A dermatoscopic image of a skin lesion: 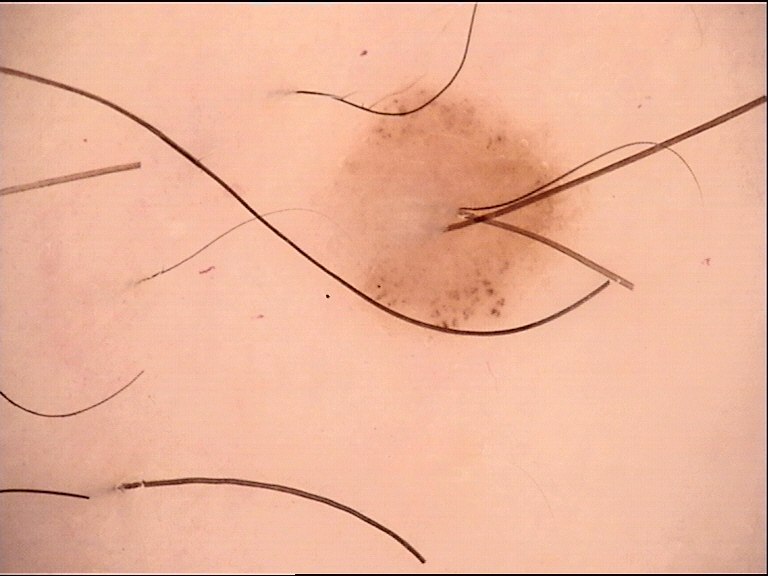label: compound nevus (expert consensus)